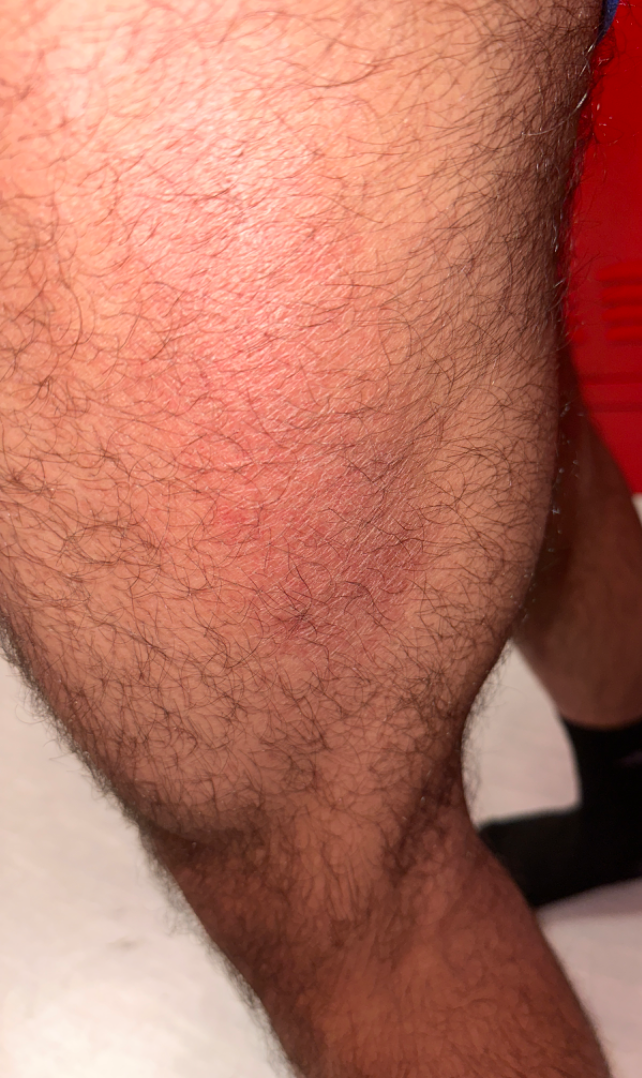Located on the leg and arm.
The photograph was taken at a distance.
The subject is 18–29, male.
Most consistent with Eczema; also consider Irritant Contact Dermatitis.